A skin lesion imaged with a dermatoscope: 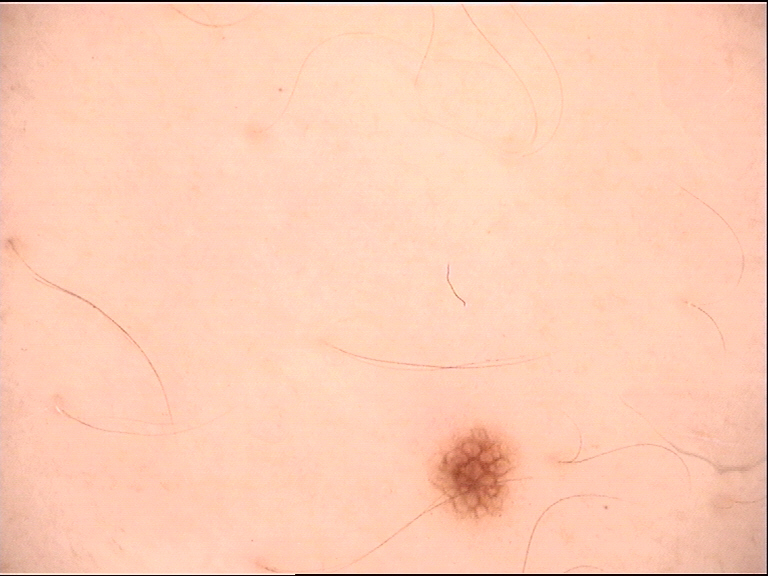Labeled as a dysplastic junctional nevus.